A clinical photograph of a skin lesion · a female subject in their 30s — 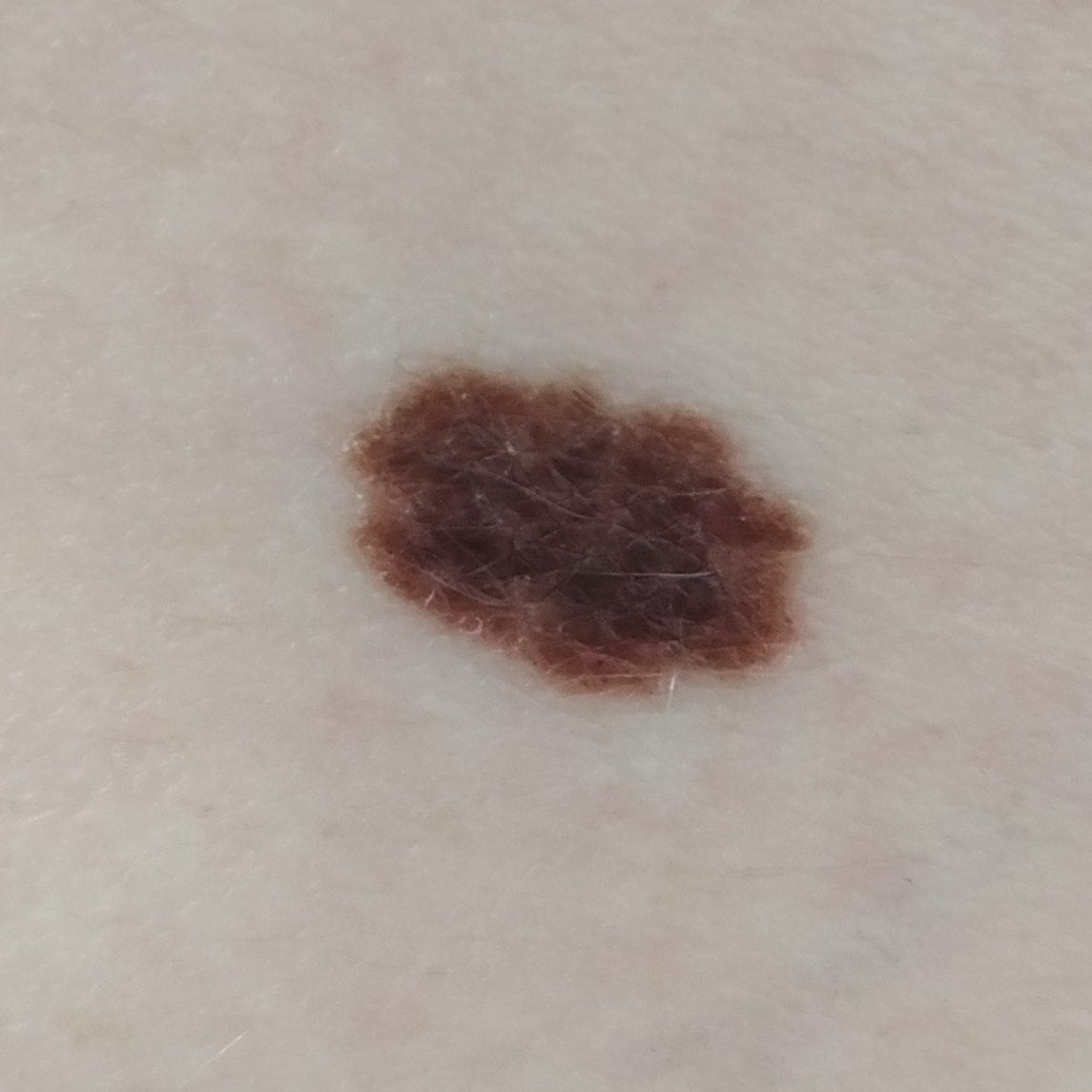site=the back
symptoms=no elevation
diagnostic label=nevus (biopsy-proven)